The chart records prior malignancy (patient or family) and prior skin cancer (patient or family); a female subject in their early 60s; the patient is Fitzpatrick II; a smartphone photograph of a skin lesion — 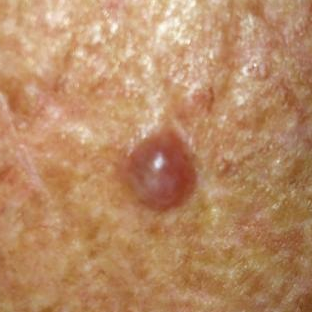The lesion is roughly 7 by 6 mm. The patient reports that the lesion hurts, itches, is elevated, and has grown, but has not changed and has not bled. Histopathological examination showed a basal cell carcinoma.